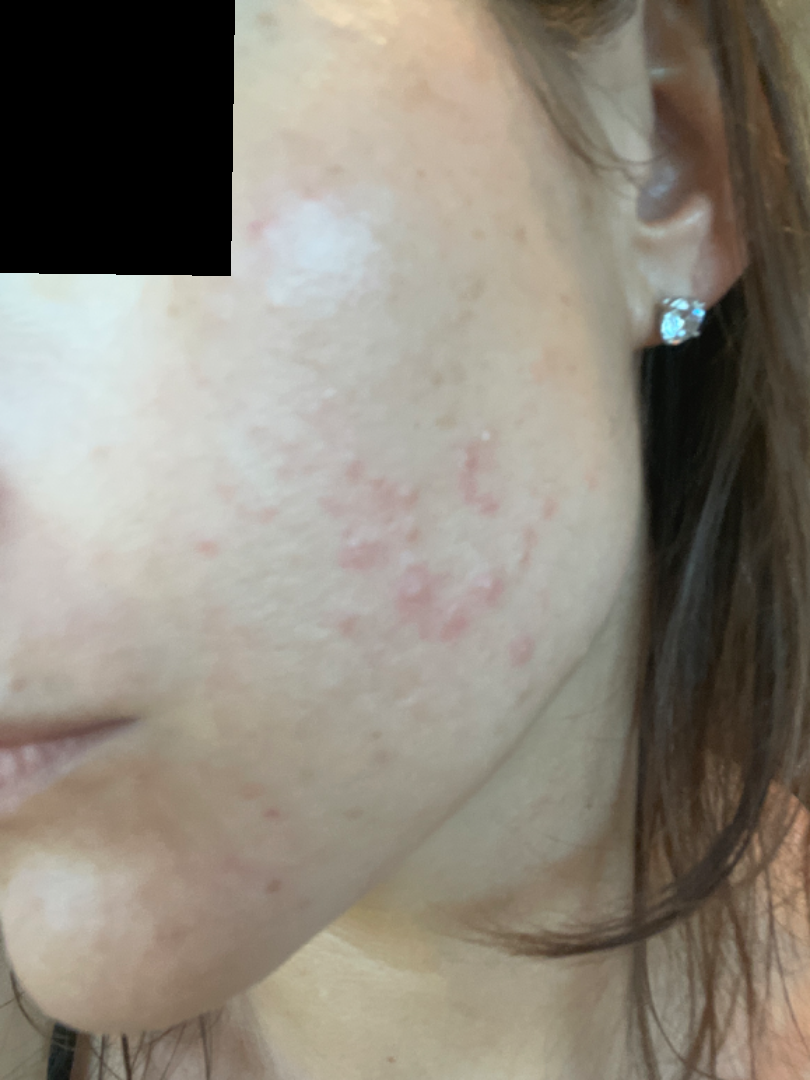Close-up view.
Reported duration is about one day.
On teledermatology review: the leading consideration is Acne; possibly Rosacea; also consider Perioral Dermatitis.